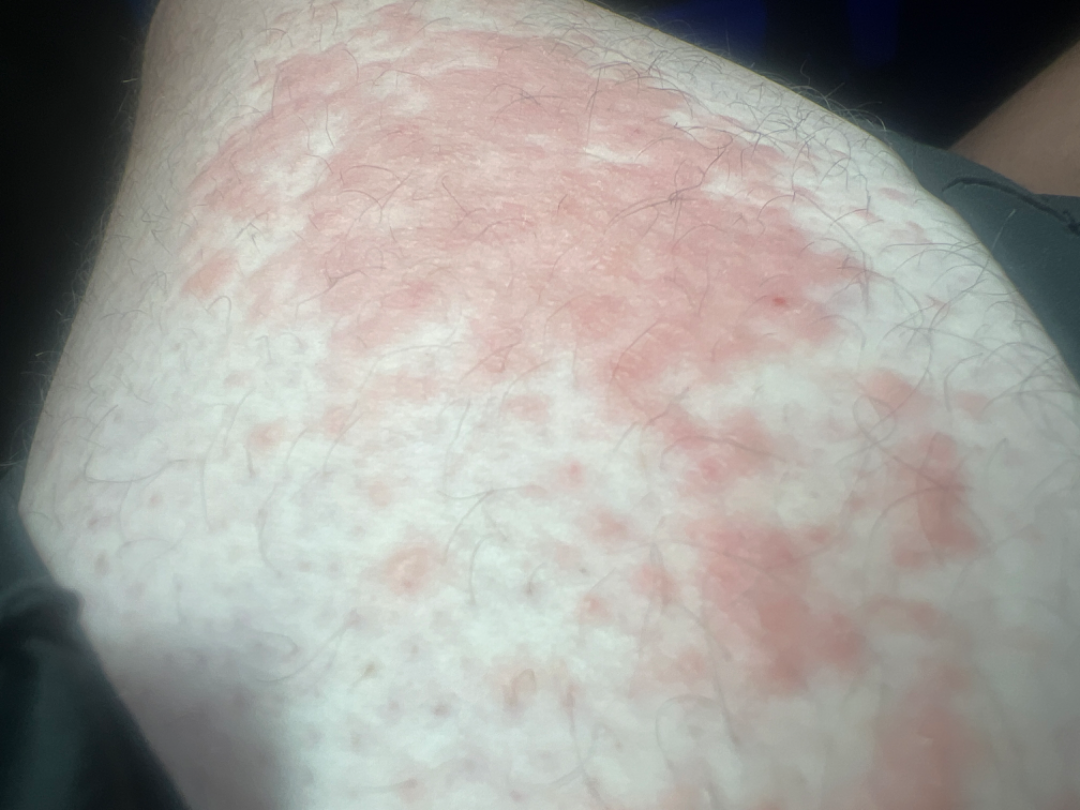Q: What is the differential diagnosis?
A: in keeping with Acute dermatitis, NOS